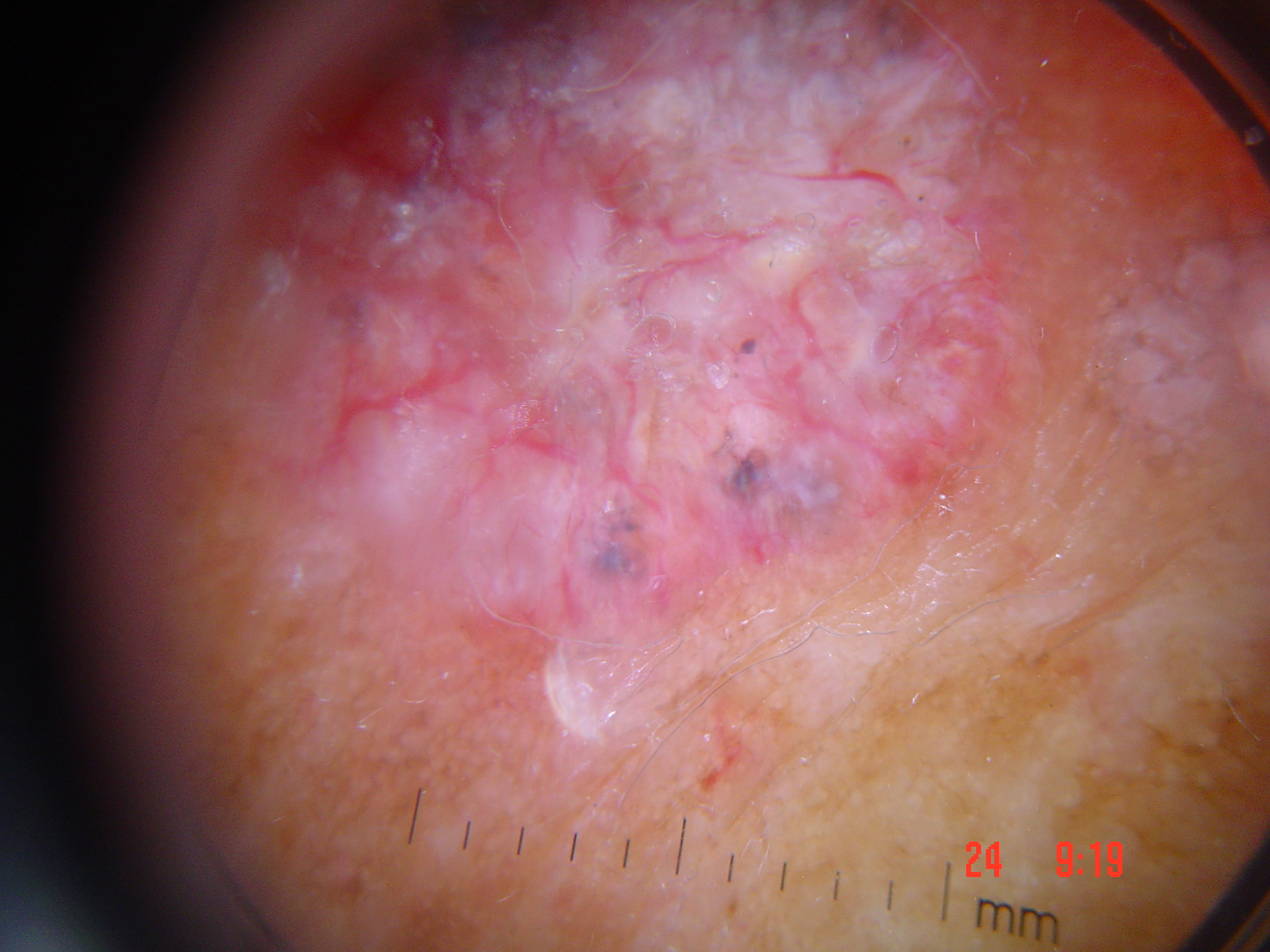Confirmed on histopathology as a basal cell carcinoma.